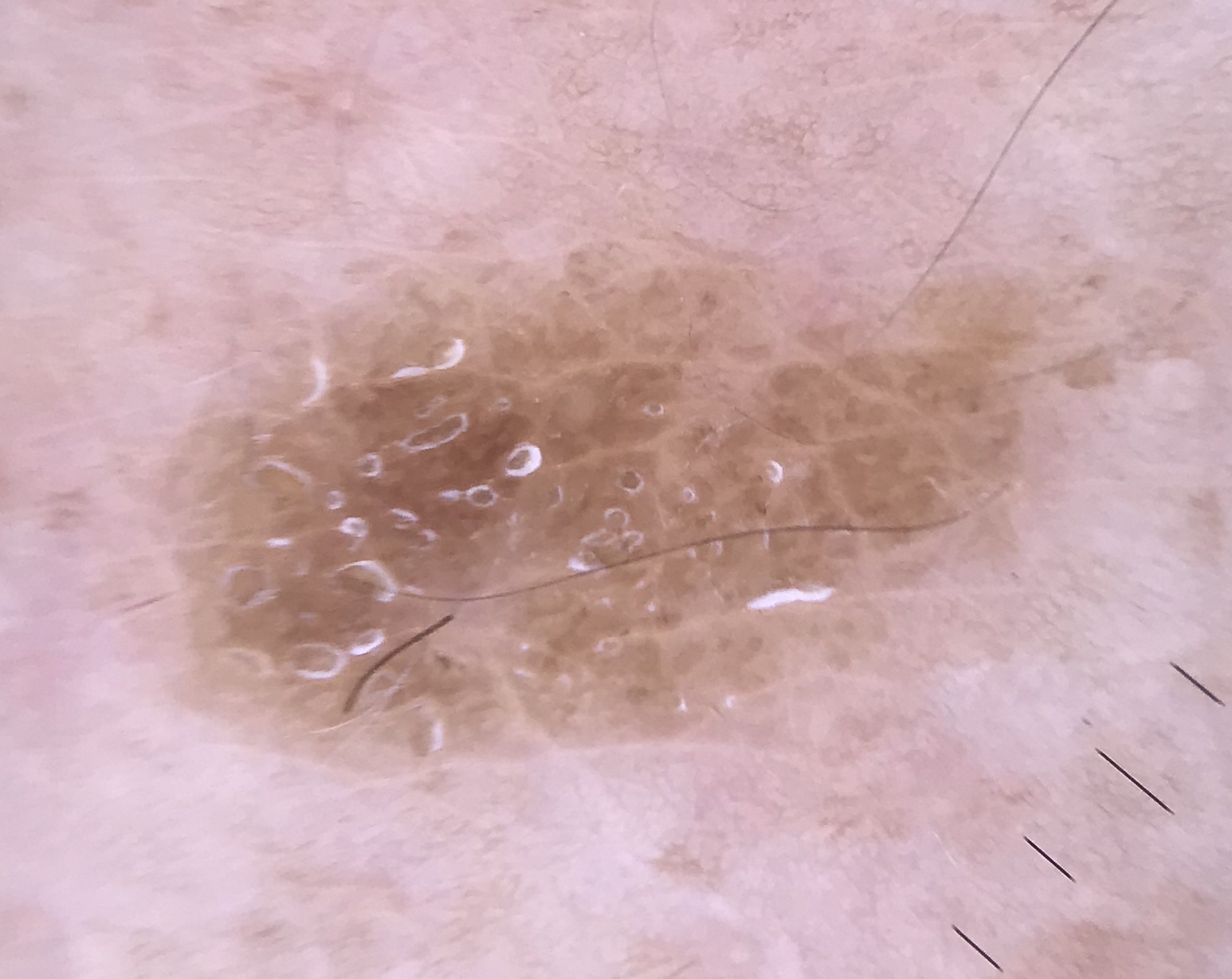This is a keratinocytic lesion.
Labeled as a seborrheic keratosis.